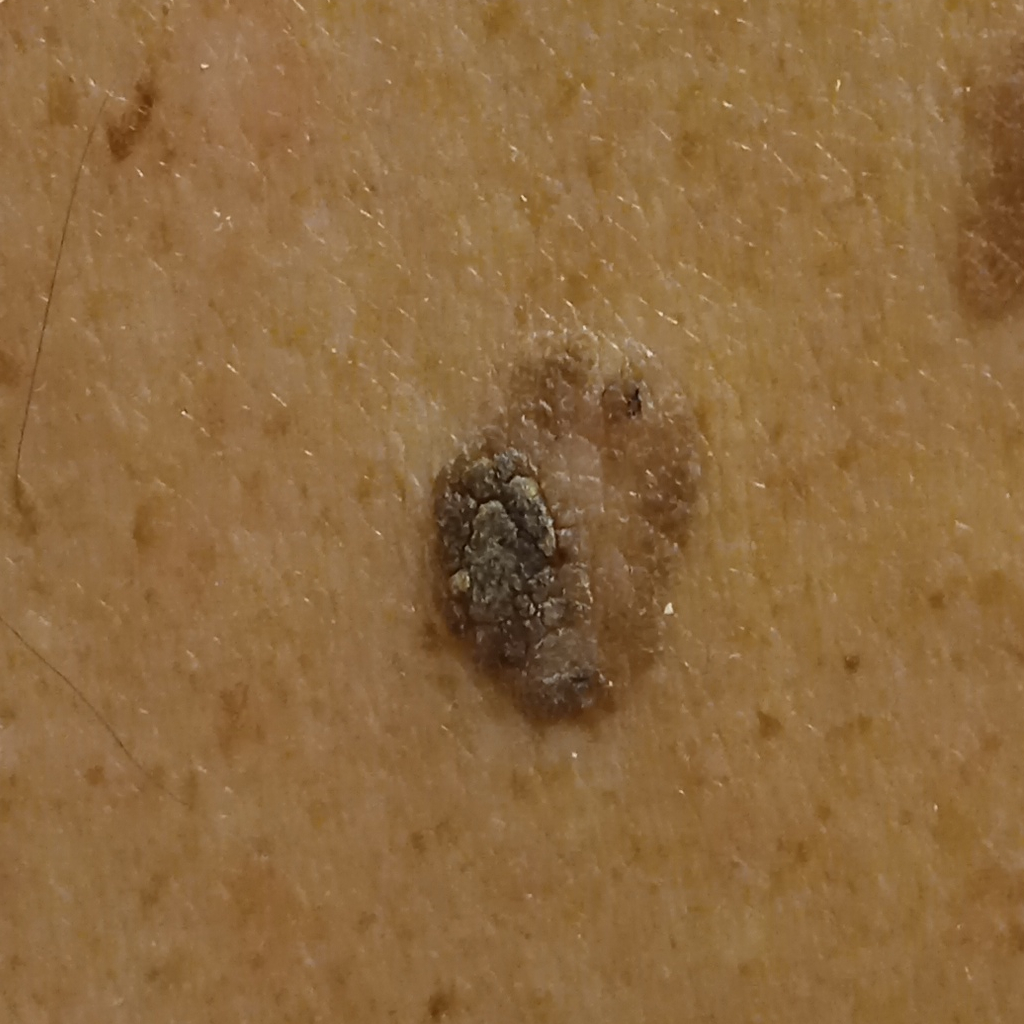Case summary:
Acquired for a research image collection, with no referral diagnosis. The patient says their skin reddens with sun exposure. A clinical close-up of a skin lesion. A male patient age 72. The patient reports a personal history of cancer and no family history of skin cancer. The patient describes having few moles overall. The lesion is located on the back.
Assessment:
The consensus diagnosis for this lesion was a seborrheic keratosis.